A skin lesion imaged with a dermatoscope.
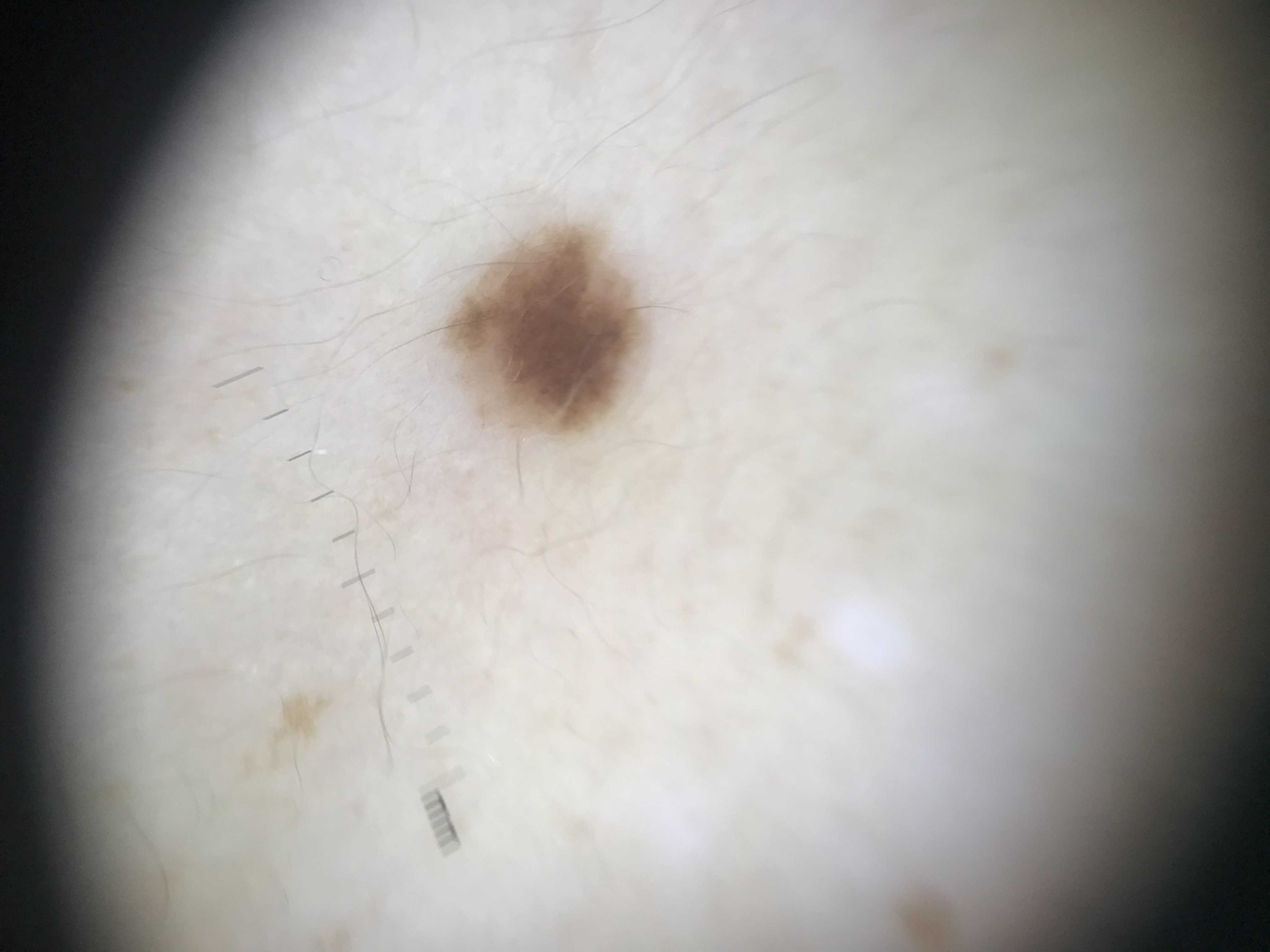Case:
- lesion type: banal
- class: junctional nevus (expert consensus)